History notes prior malignancy (patient or family). A female subject age 70. FST II — 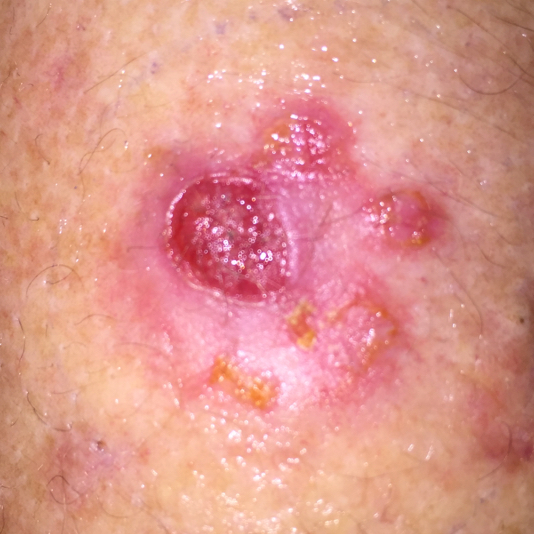The lesion was found on an arm. The lesion measures approximately 24 × 20 mm. The patient reports that the lesion has grown, itches, has bled, and hurts. The biopsy diagnosis was a squamous cell carcinoma.